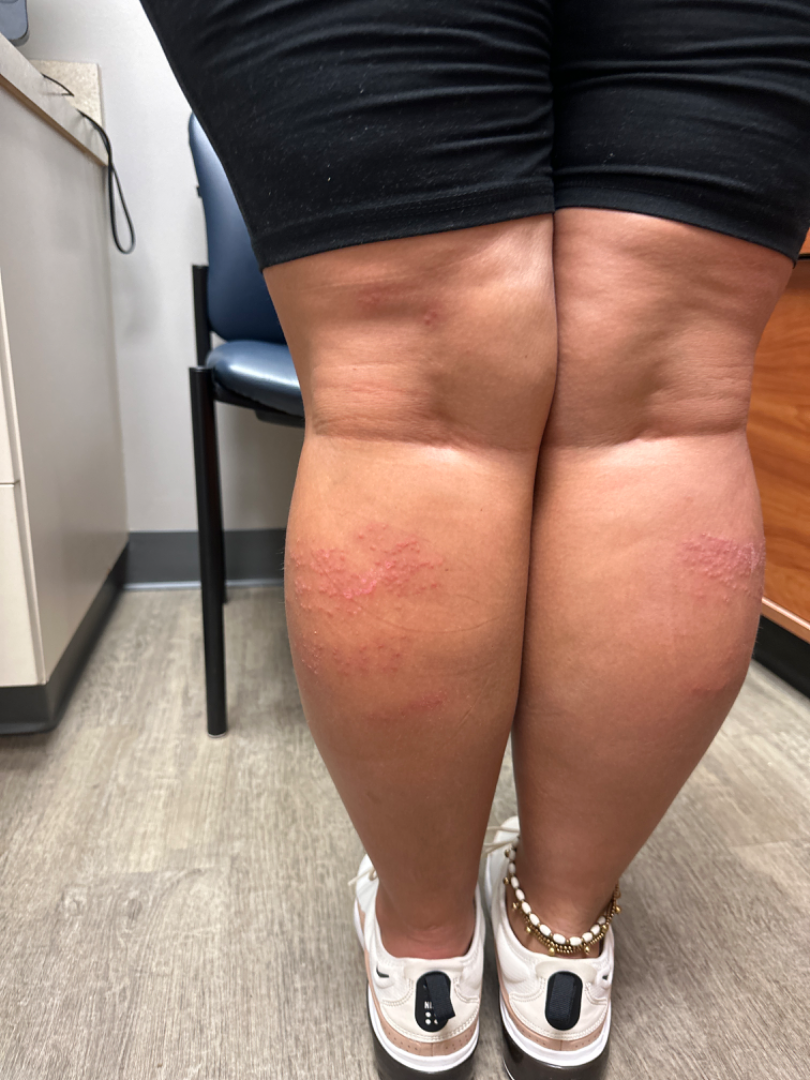The case was difficult to assess from the available photograph.
The lesion is associated with itching and burning.
Present for less than one week.
The contributor reports the lesion is rough or flaky and raised or bumpy.
The affected area is the leg.
Fitzpatrick III; lay graders estimated MST 3.
An image taken at a distance.